A male patient 30 years of age. A clinical photo of a skin lesion taken with a smartphone. Recorded as Fitzpatrick phototype II: 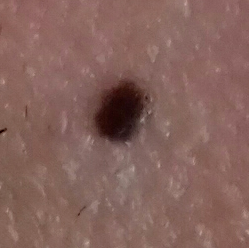location: the neck, size: 20 × 20 mm, patient-reported symptoms: no pain, diagnosis: melanoma (biopsy-proven).